Dermoscopy of a skin lesion; the patient says their skin tans without first burning; collected as part of a research study, without a referral diagnosis; the patient describes having numerous moles; a female subject 78 years old:
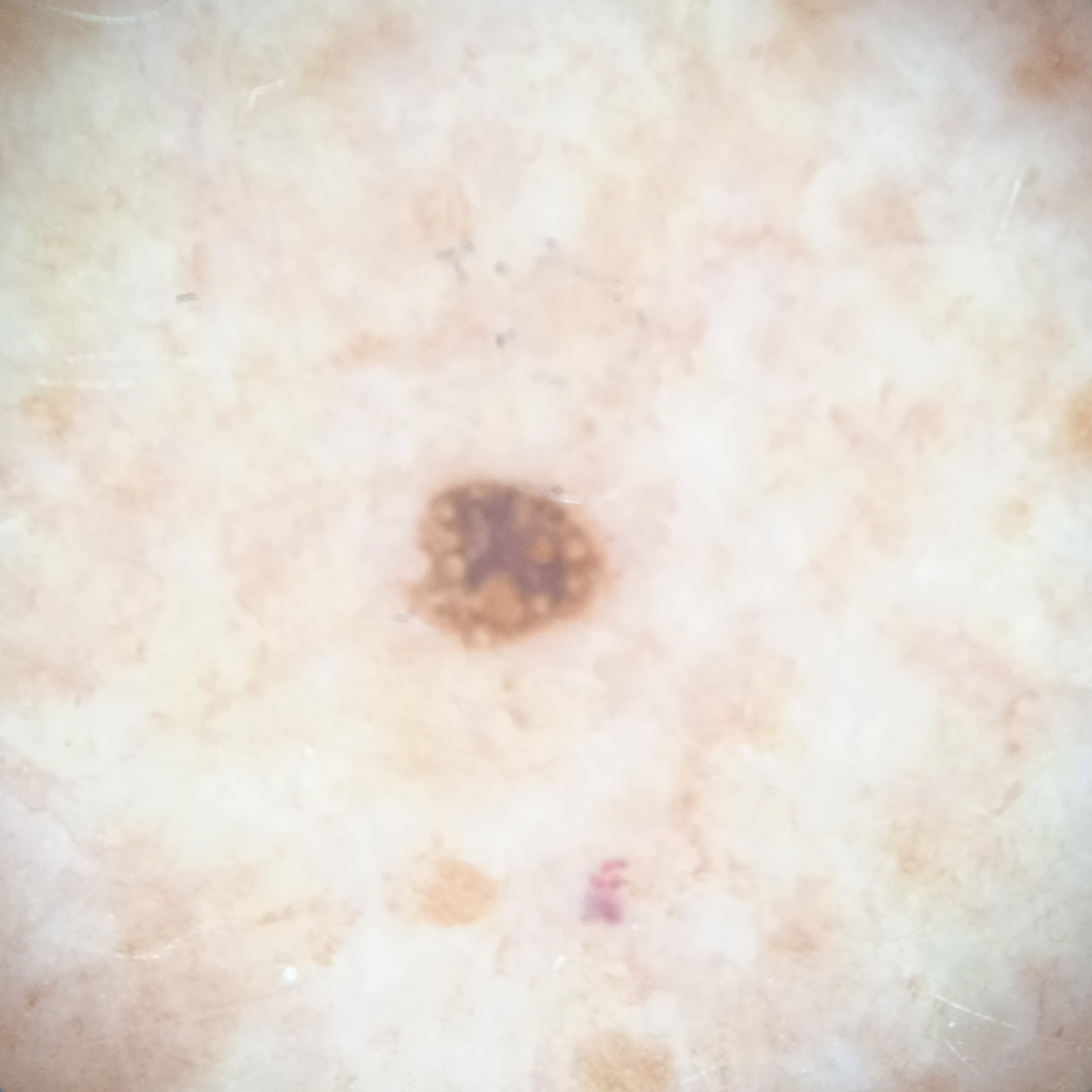{
  "lesion_location": "an arm",
  "lesion_size": {
    "diameter_mm": 2.4
  },
  "diagnosis": {
    "name": "seborrheic keratosis",
    "malignancy": "benign"
  }
}